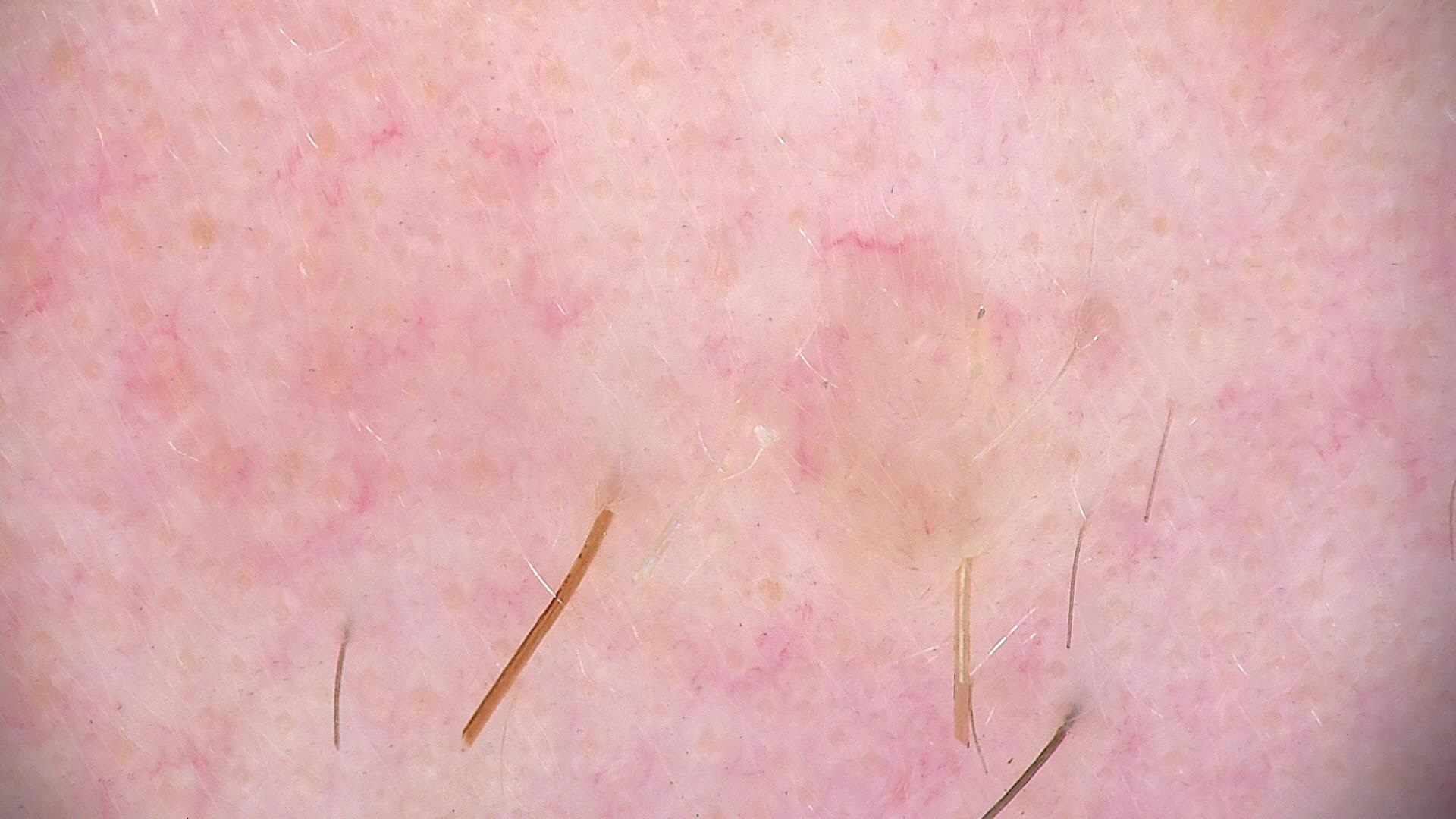Q: What is this lesion?
A: dermal nevus (expert consensus)